The photo was captured at a distance. The affected area is the head or neck.
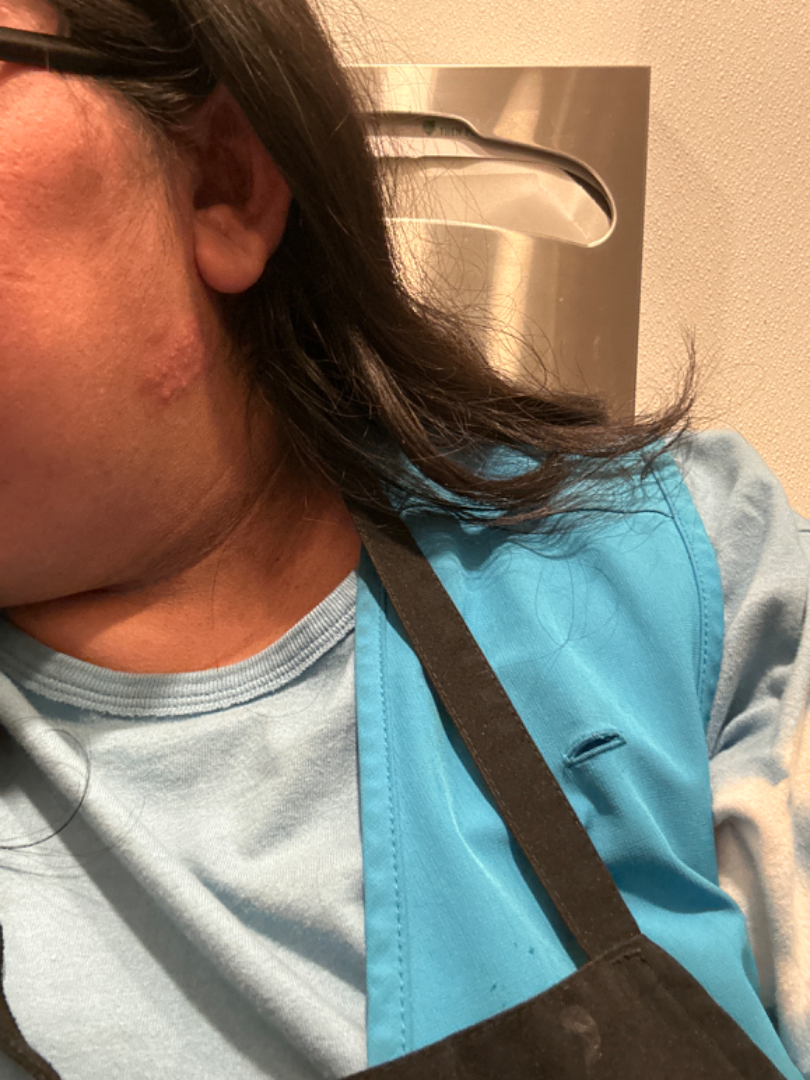Assessment:
On photographic review, in keeping with Herpes Simplex.